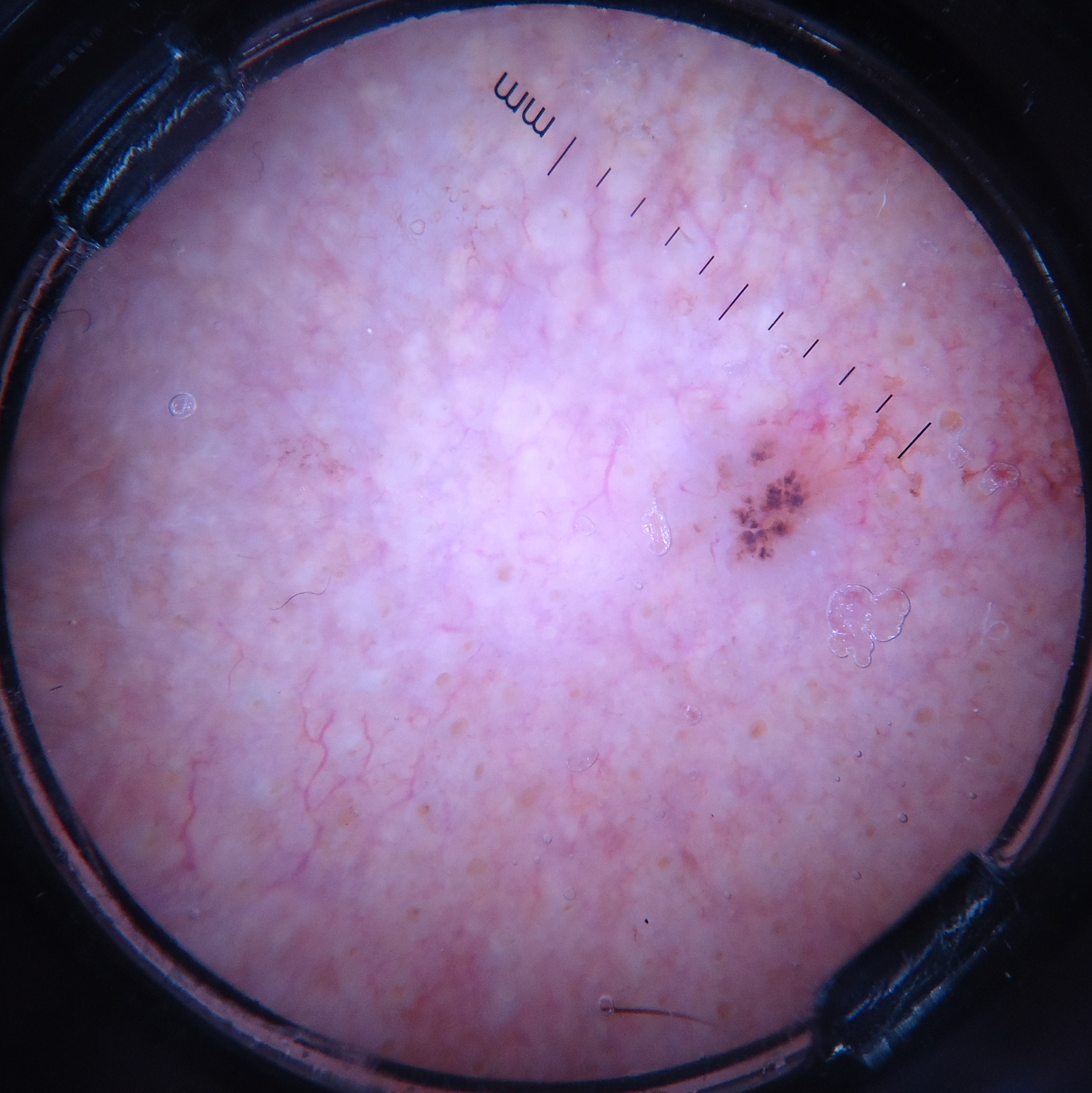* classification: keratinocytic
* label: basal cell carcinoma (biopsy-proven)